A clinical close-up photograph of a skin lesion. A subject age 72 — 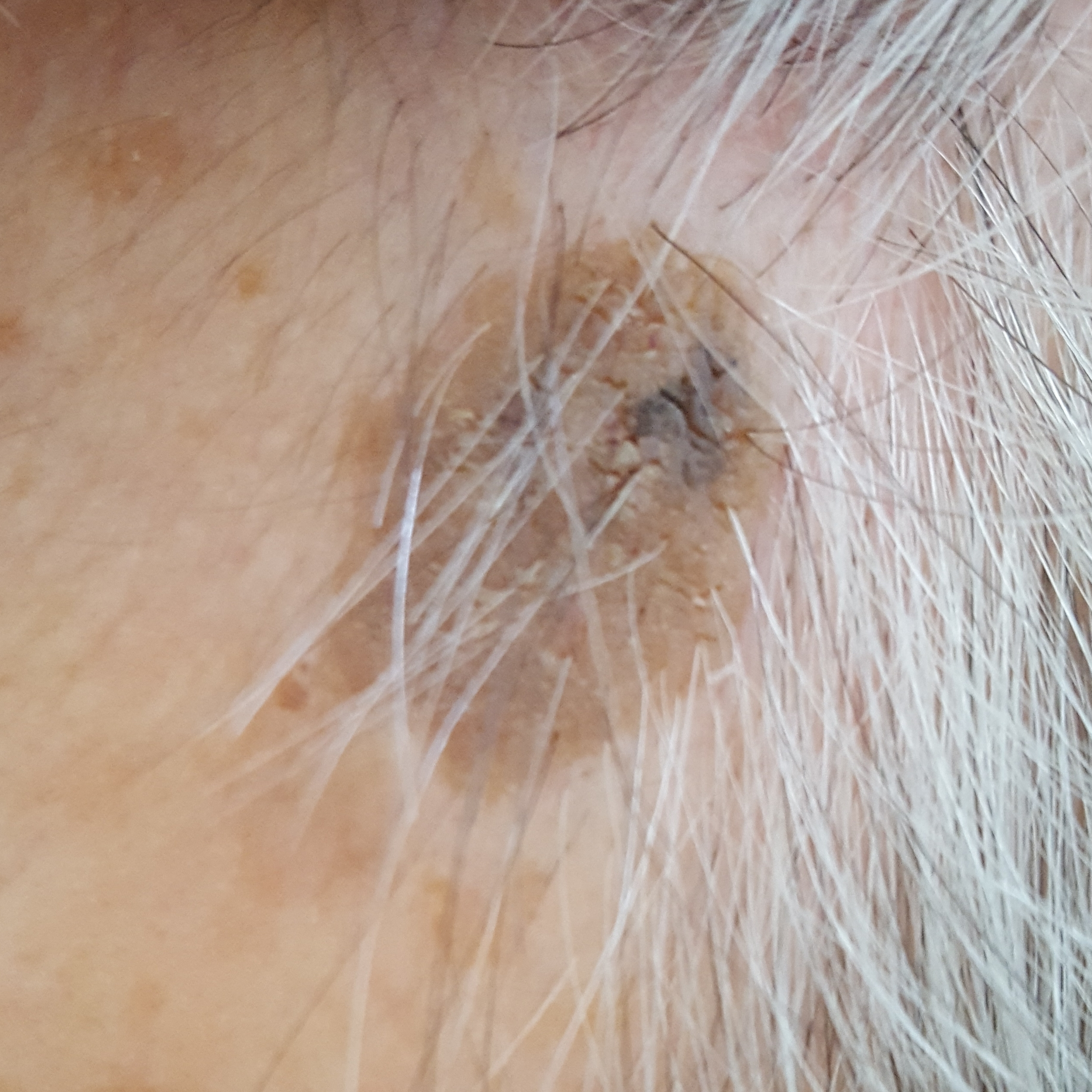Case summary: The lesion is on the face. Conclusion: Consistent with a seborrheic keratosis.